A dermatoscopic image of a skin lesion, the subject is a female aged approximately 45 — 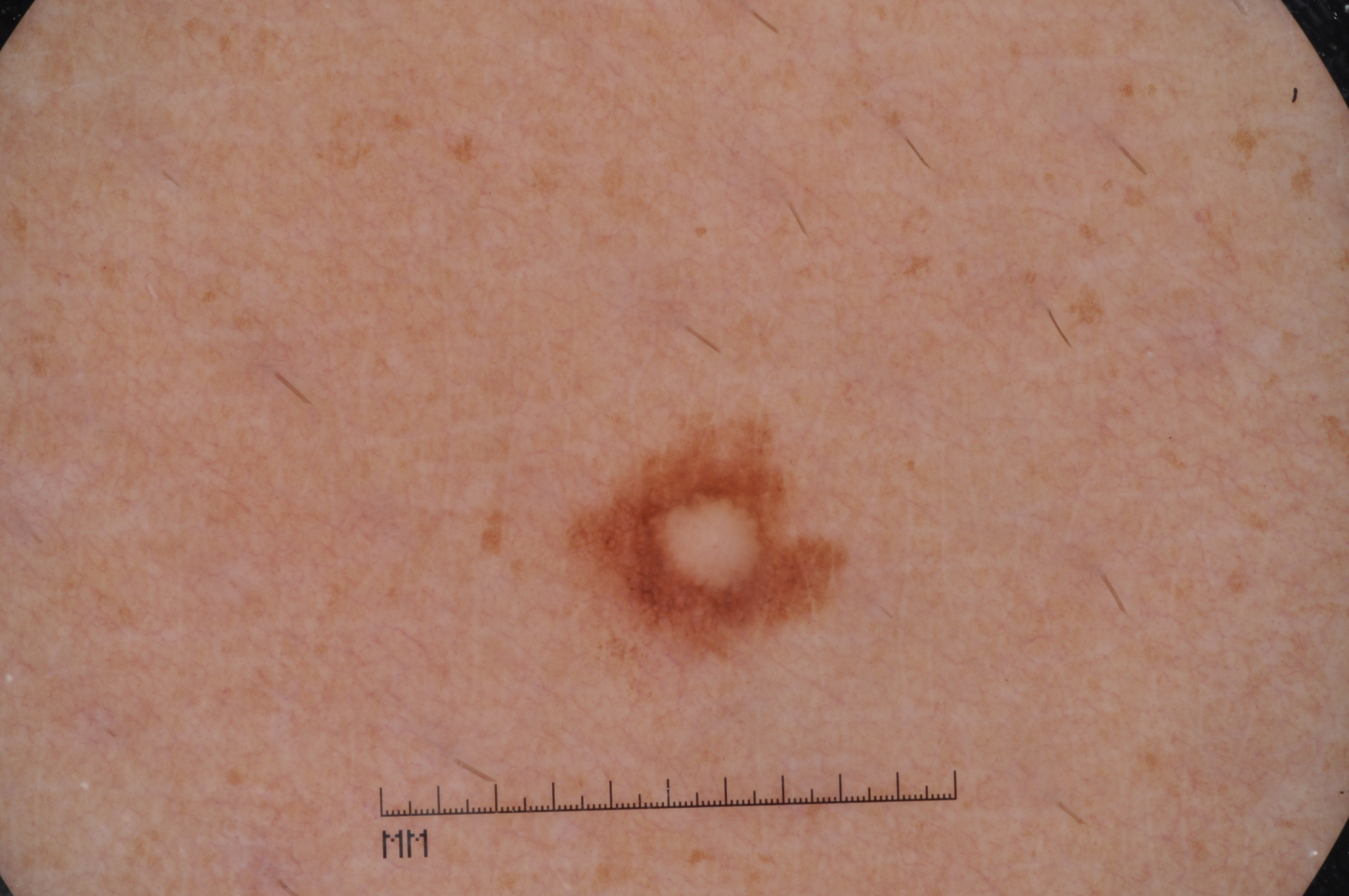Summary: The lesion occupies roughly 4% of the field. With coordinates (x1, y1, x2, y2), the lesion spans 555 412 850 673. On dermoscopy, the lesion shows pigment network, with no milia-like cysts, streaks, or negative network. Impression: The clinical diagnosis was a melanocytic nevus, a benign lesion.